A dermoscopic image of a skin lesion: 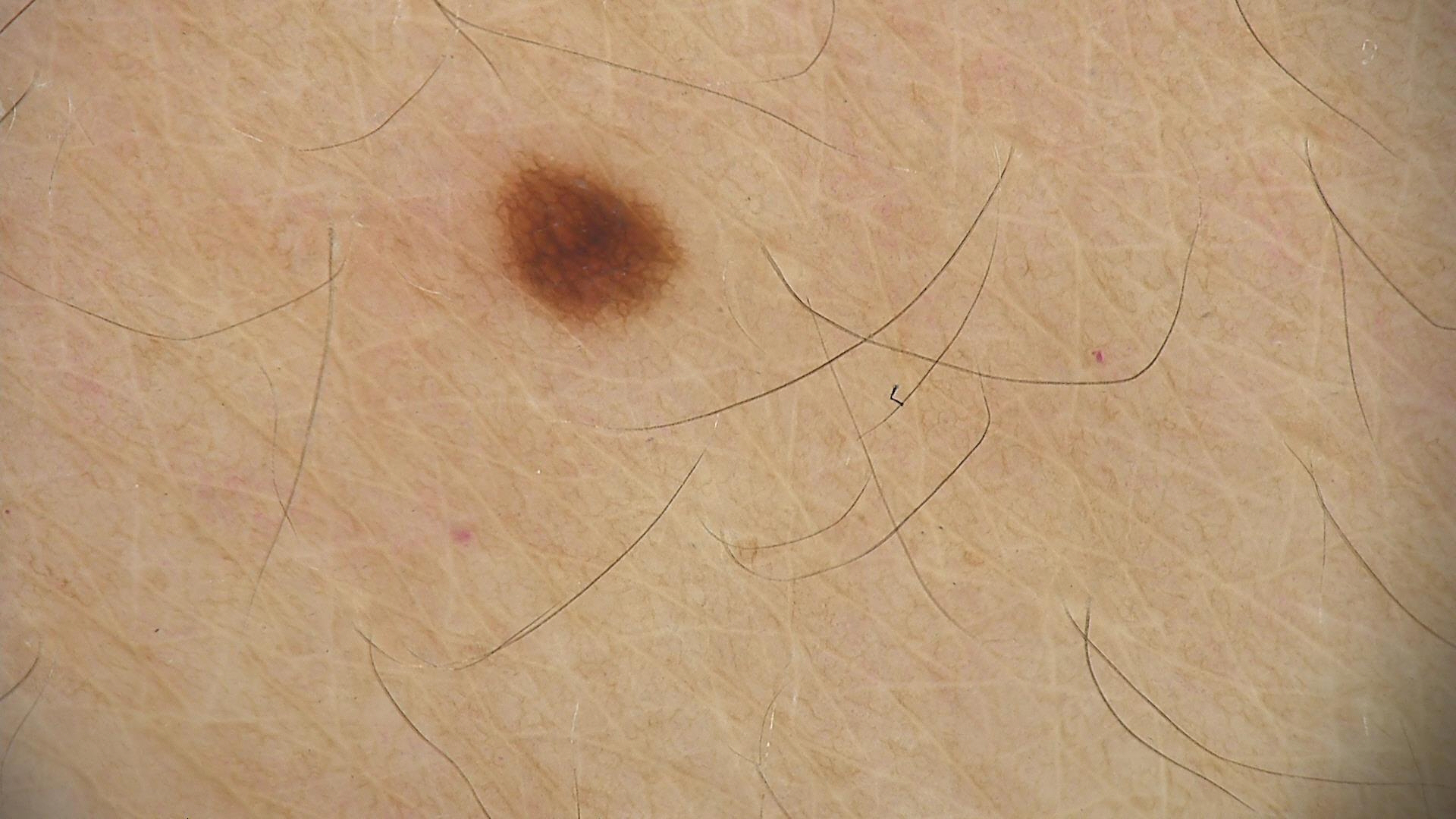• diagnostic label · dysplastic junctional nevus (expert consensus)